A female subject, approximately 50 years of age. A dermatoscopic image of a skin lesion: 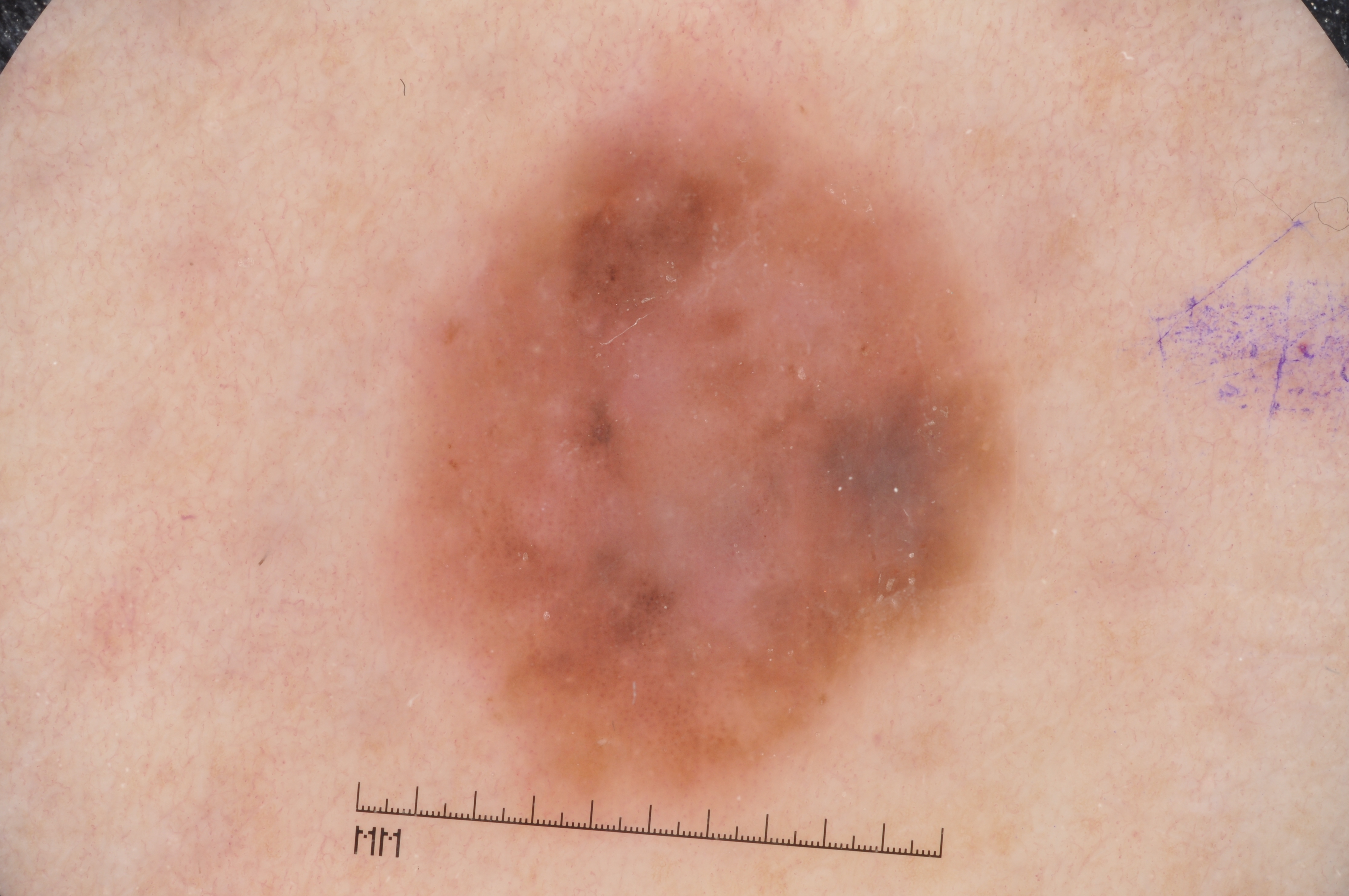| key | value |
|---|---|
| lesion location | <box>377, 72, 1040, 823</box> |
| dermoscopic findings | milia-like cysts |
| lesion extent | ~32% of the field |
| diagnosis | a melanoma, a malignant skin lesion |